History notes prior malignancy (patient or family) and prior skin cancer (patient or family); a clinical photograph showing a skin lesion; the patient is FST I; a male subject age 77: 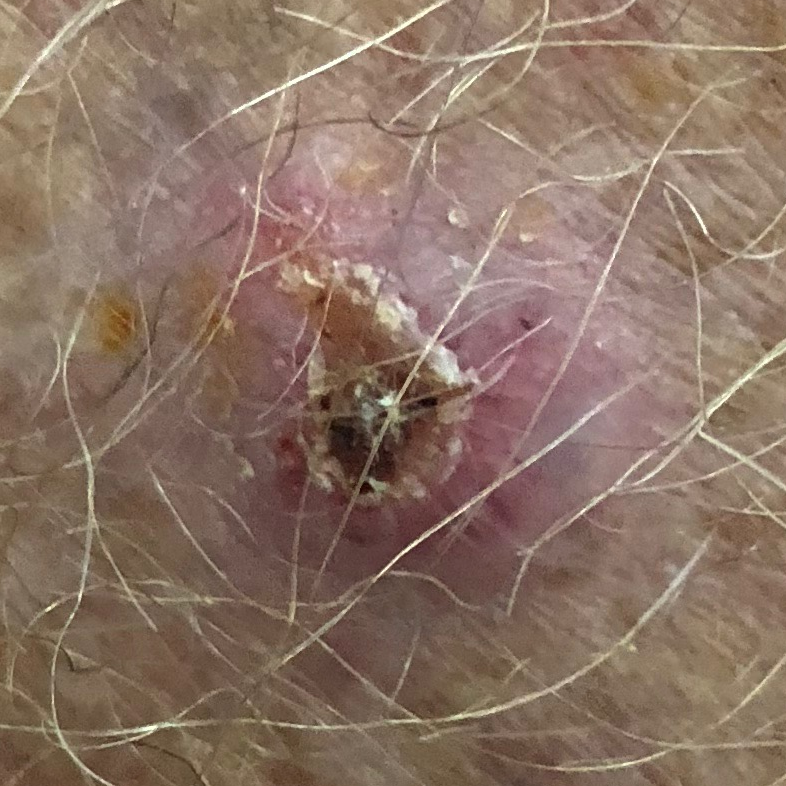Summary: The lesion involves a forearm. Per patient report, the lesion itches, has bled, hurts, and is elevated. Diagnosis: Histopathology confirmed a basal cell carcinoma.